A skin lesion imaged with a dermatoscope.
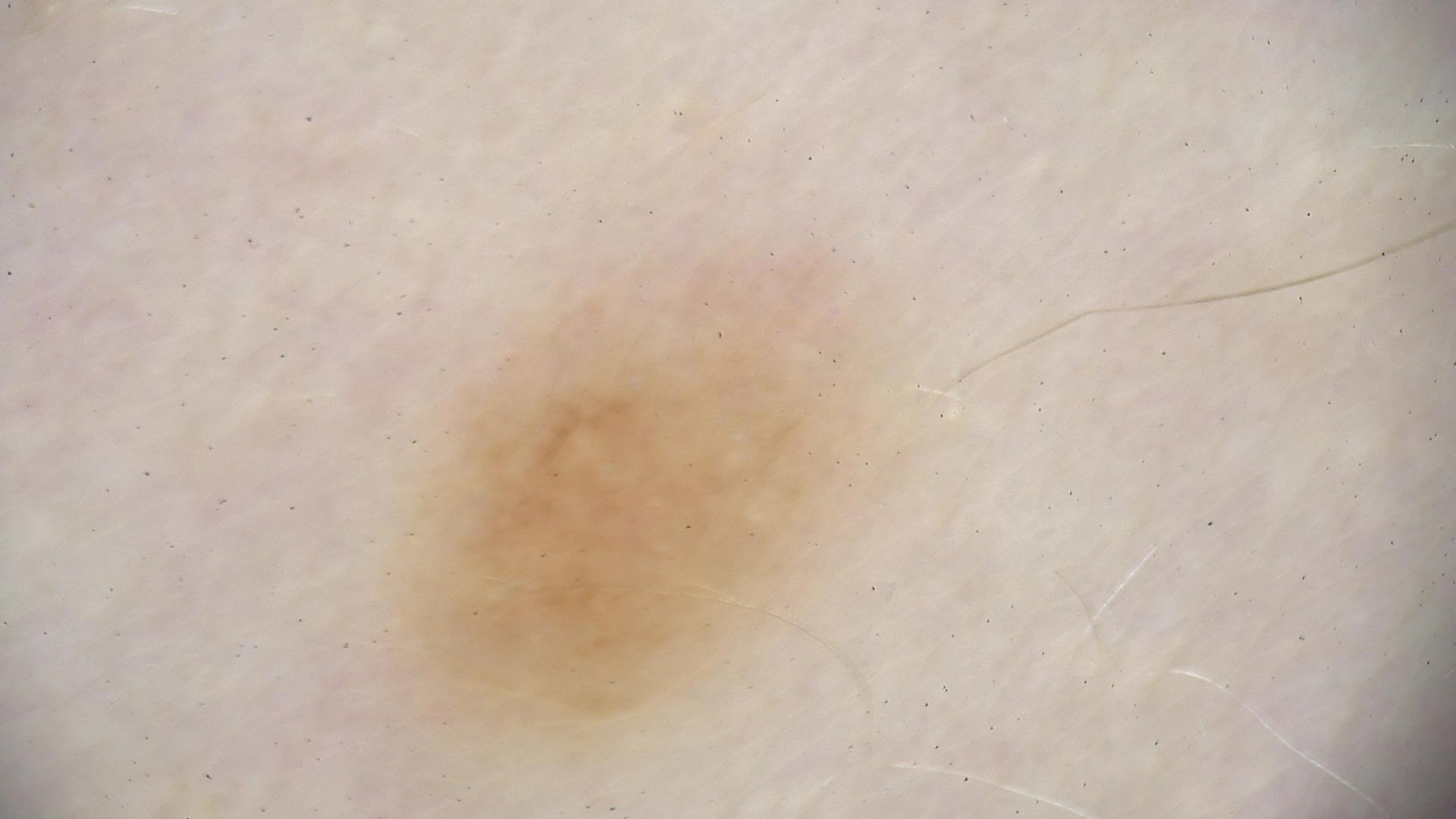classification — banal; class — junctional nevus (expert consensus).